A wide-field clinical photograph of a skin lesion; the patient was assessed as Fitzpatrick II; a male subject aged 58-62:
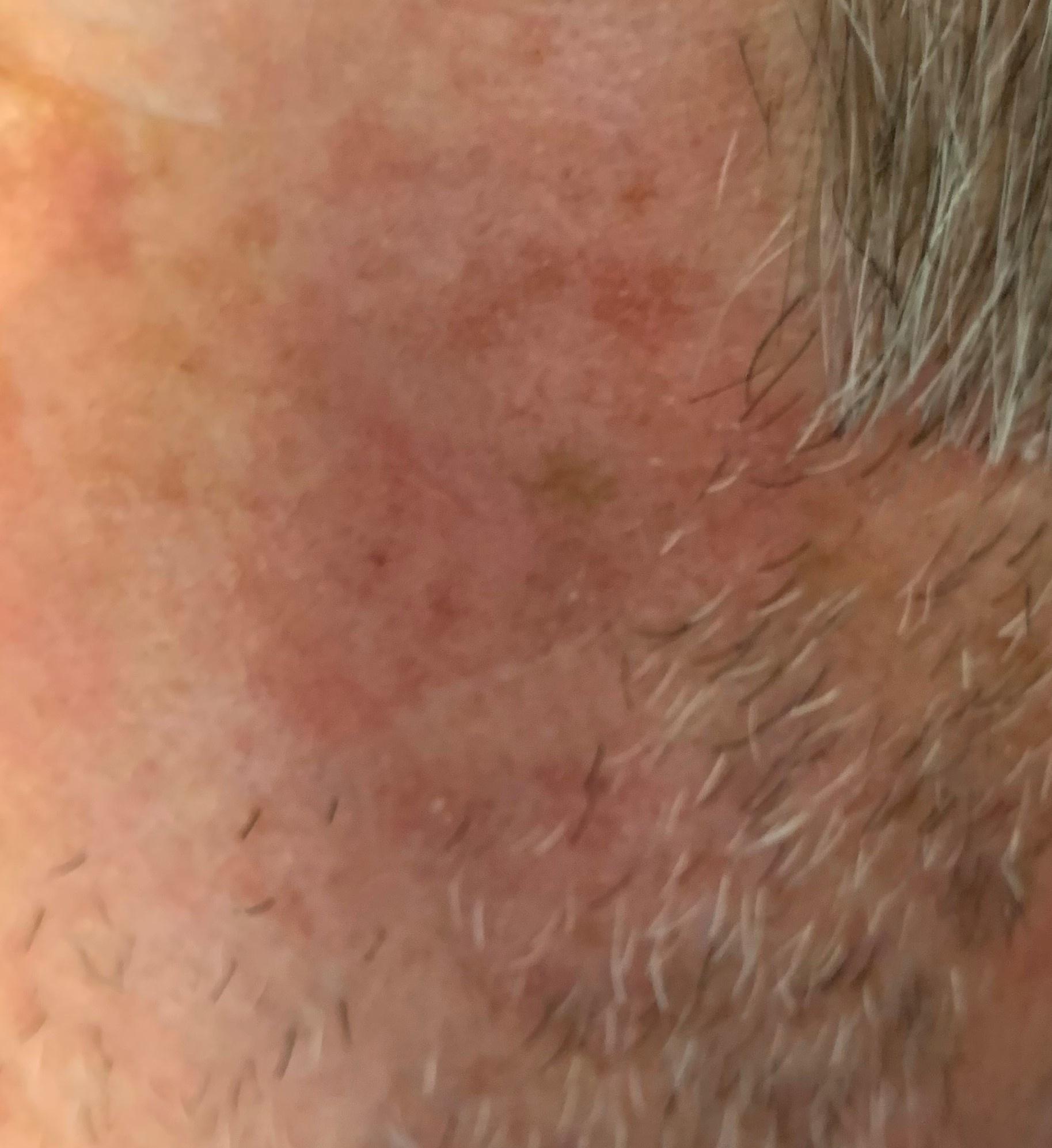Consistent with an epidermal proliferation — a solar or actinic keratosis.